Symptoms reported: burning, pain and itching. The condition has been present for about one day. The affected area is the arm. The contributor notes the lesion is raised or bumpy. The patient described the issue as a rash. Female patient, age 60–69. This image was taken at an angle: 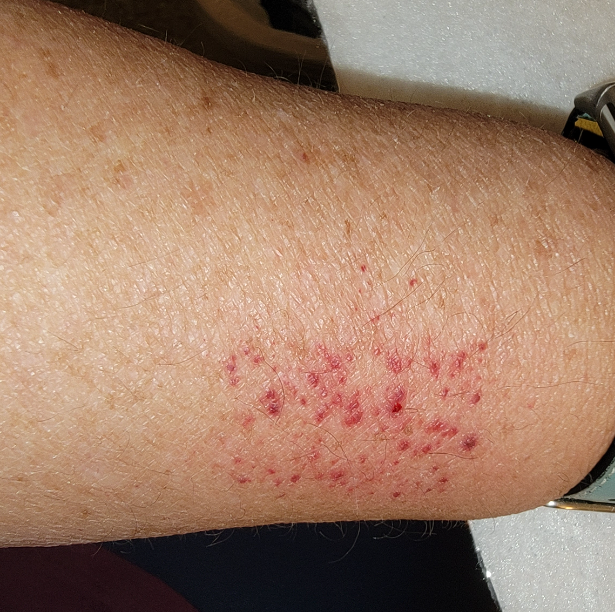differential:
  tied_lead:
    - Contact purpura
    - Purpura
  unlikely:
    - Vasculitis of the skin, NOS